A skin lesion imaged with a dermatoscope.
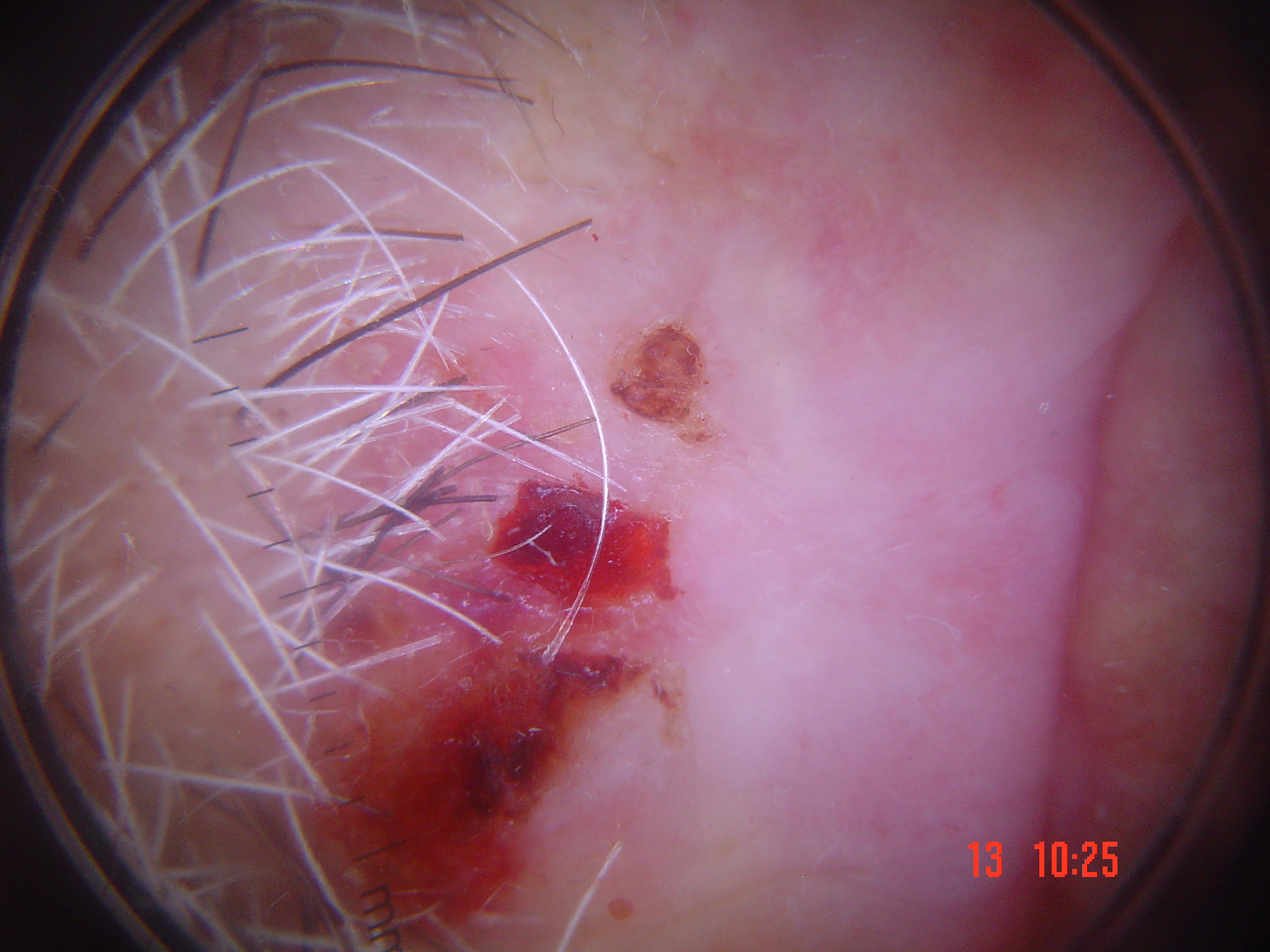Case:
The architecture is that of a keratinocytic lesion.
Diagnosis:
Histopathologically confirmed as a malignancy — a squamous cell carcinoma.